The affected area is the palm and back of the hand. Female contributor, age 40–49. Reported duration is one to four weeks. No associated systemic symptoms reported. The lesion is described as raised or bumpy. An image taken at an angle — 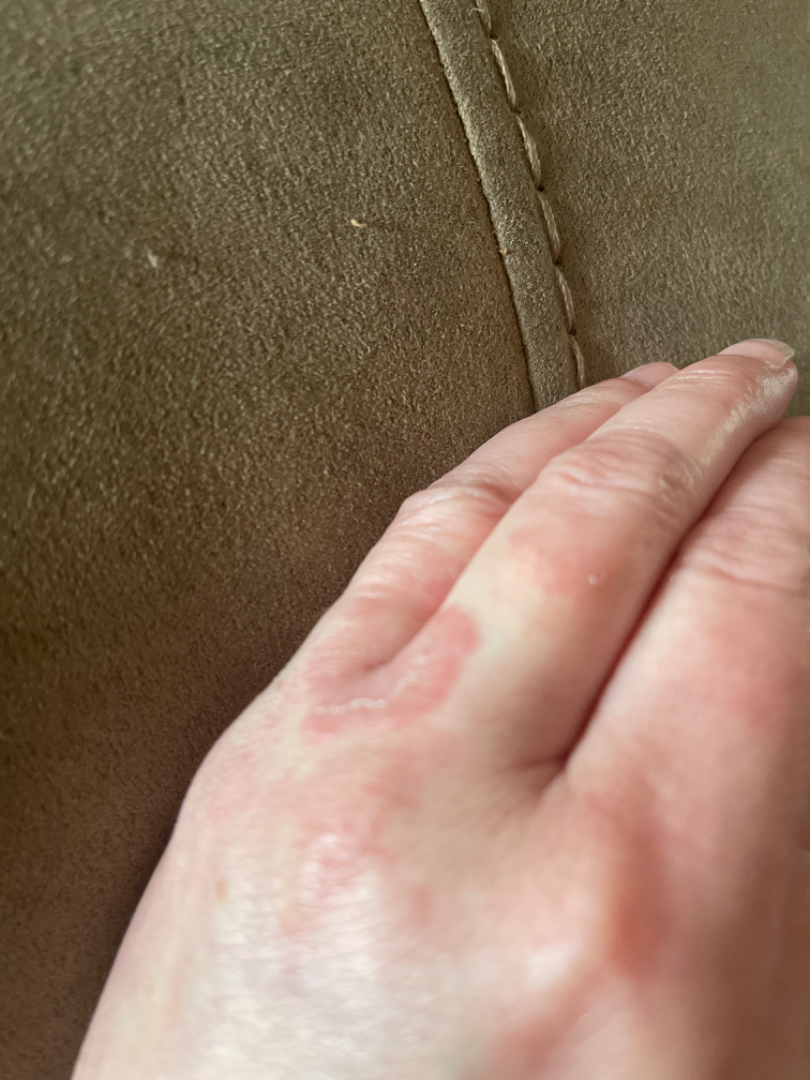<dermatology_case>
<differential>
  <leading>Granuloma annulare</leading>
</differential>
</dermatology_case>